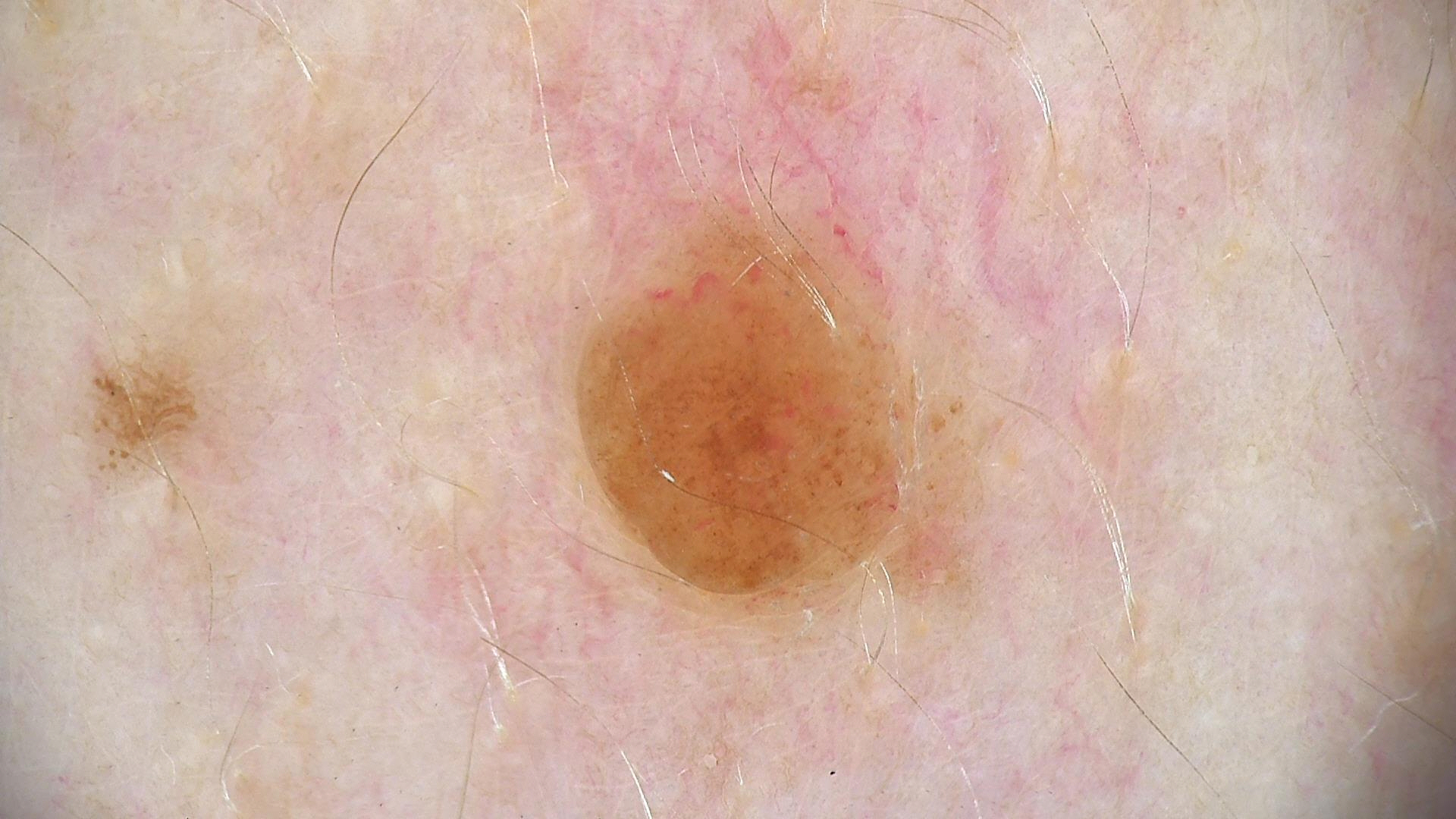image: dermatoscopy
class: dermal nevus (expert consensus)